The patient describes having a moderate number of moles; imaged for a research study, with no referral diagnosis recorded; on a questionnaire the patient reported no sunbed use; dermoscopy of a skin lesion — 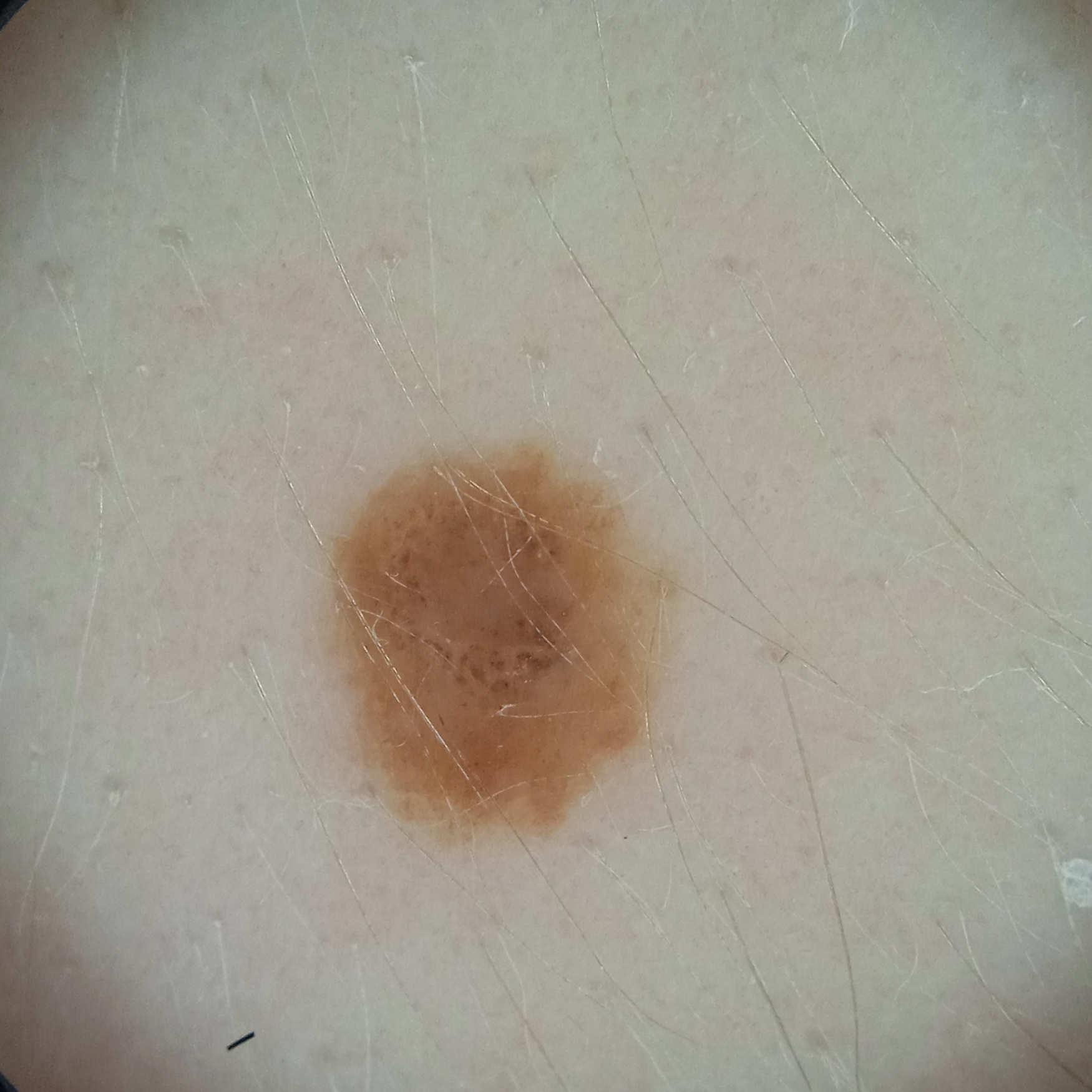The lesion is located on the torso.
The dermatologists' assessment was a melanocytic nevus.